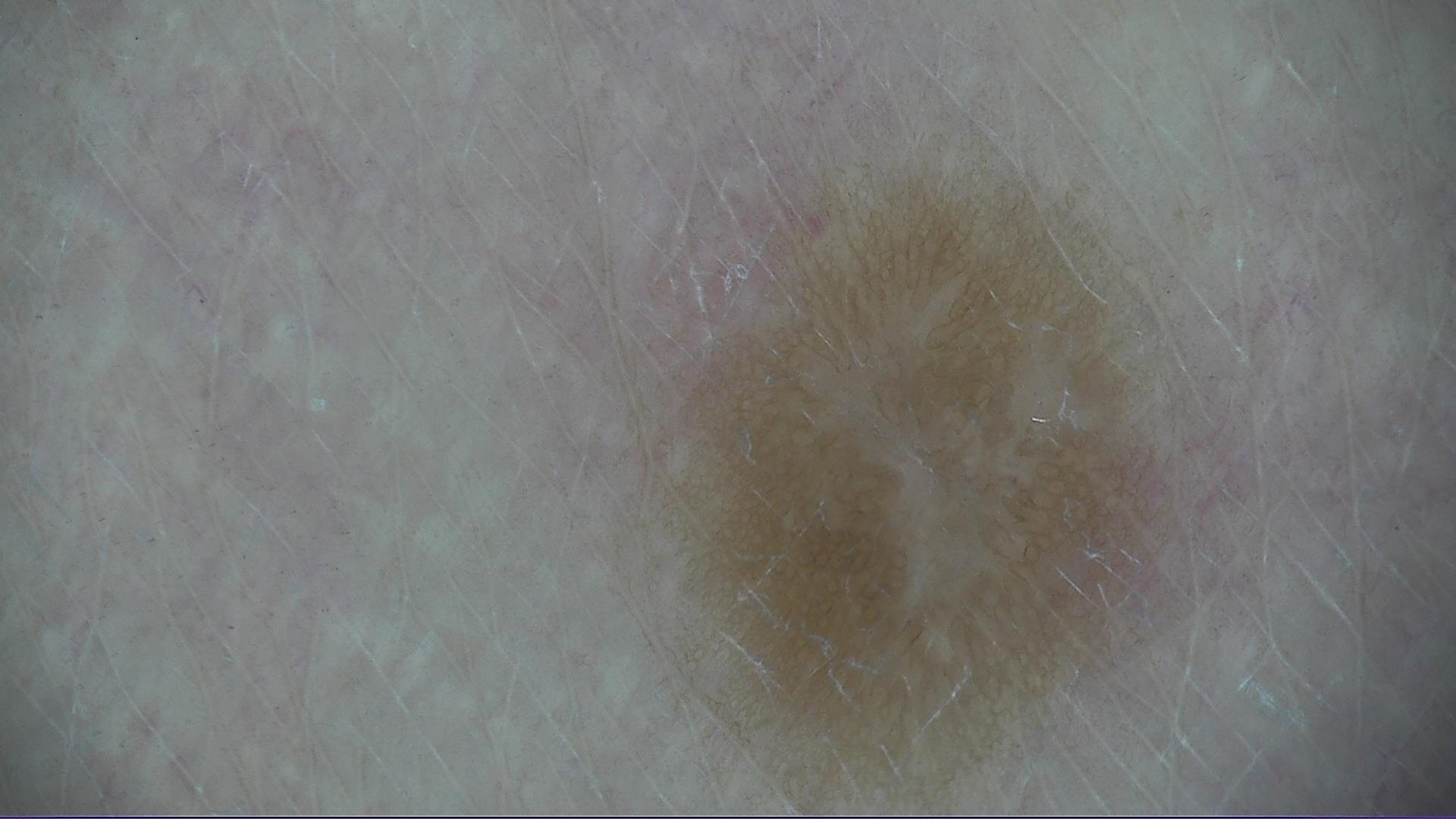diagnostic label: dermatofibroma (expert consensus)